Located on the top or side of the foot, this is a close-up image — 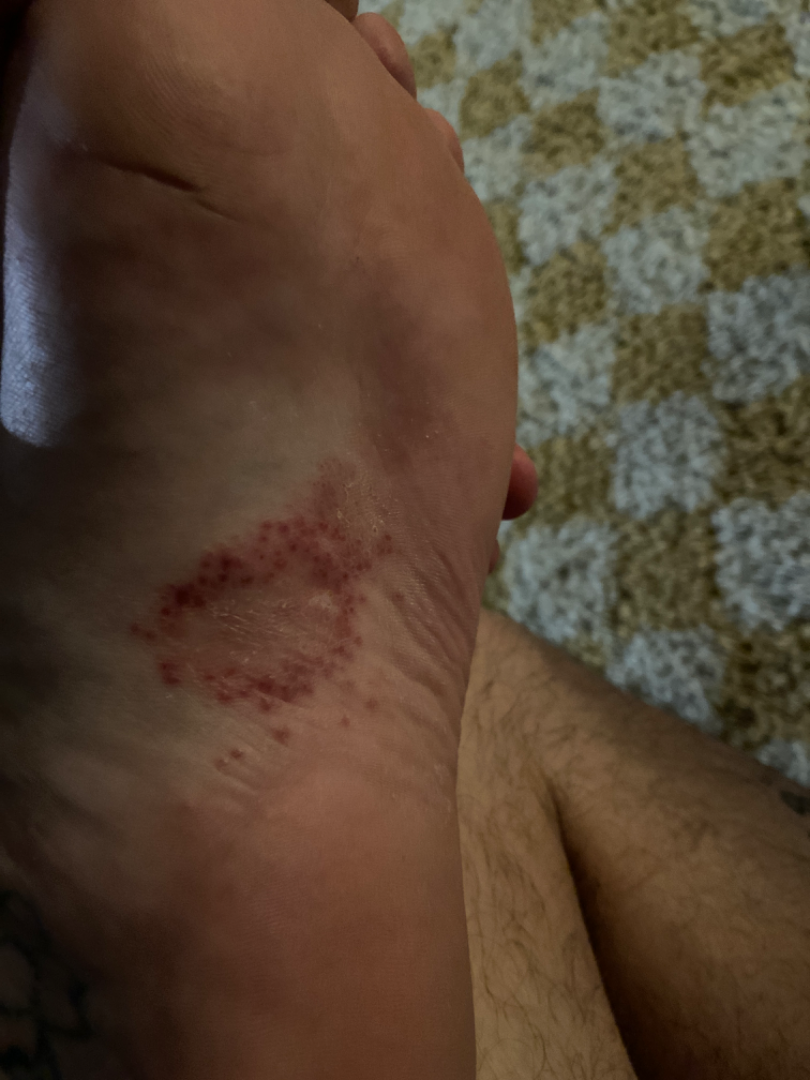Present for one to four weeks. Texture is reported as raised or bumpy. Reported lesion symptoms include bothersome appearance. The patient considered this a rash. On dermatologist assessment of the image: the primary impression is Psoriasis; with consideration of Tinea; less likely is Allergic Contact Dermatitis.